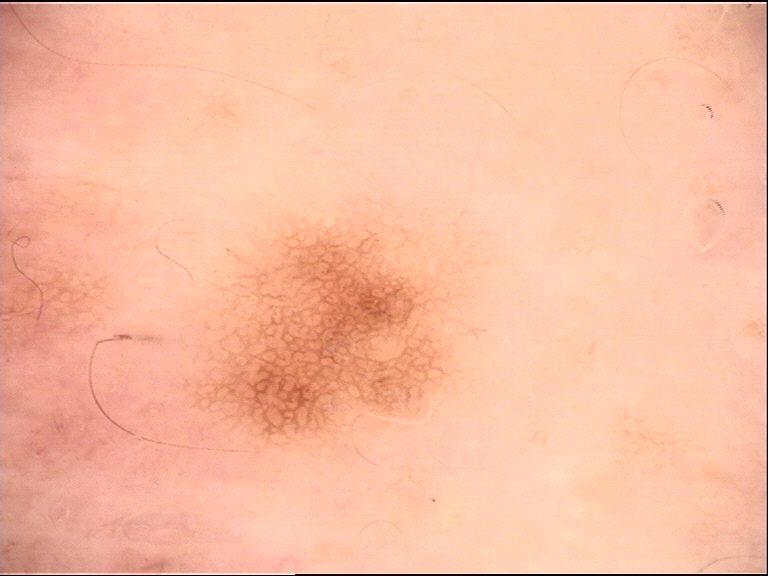modality — dermatoscopy
class — dysplastic junctional nevus (expert consensus)